A dermatoscopic image of a skin lesion · a female subject aged around 15: 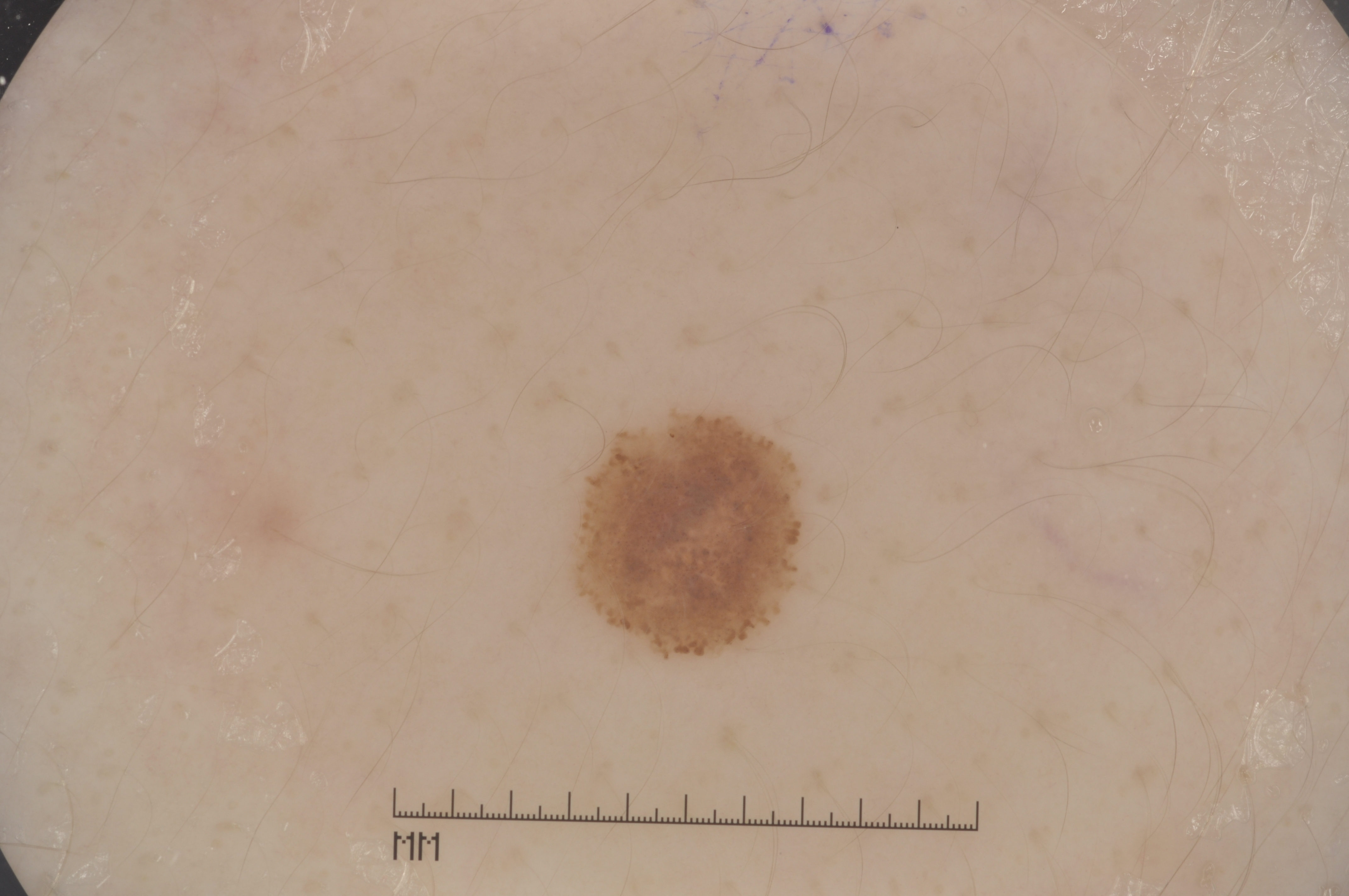Dermoscopic examination shows negative network and streaks.
The lesion spans x1=580, y1=413, x2=801, y2=658.
The diagnostic assessment was a melanocytic nevus.